The photograph was taken at an angle, texture is reported as raised or bumpy, the affected area is the arm and leg, symptoms reported: itching, the patient considered this a rash, present for less than one week.
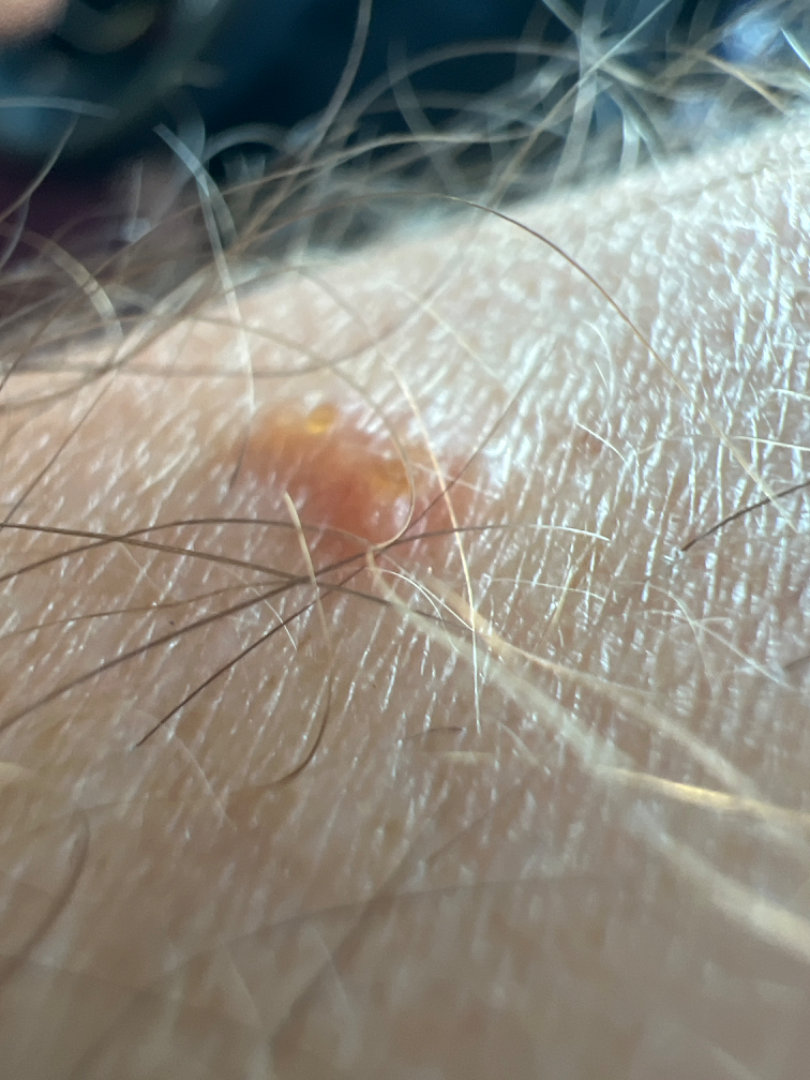<report>
<assessment>ungradable on photographic review</assessment>
</report>